A clinical photograph showing a skin lesion · referred with a clinical suspicion of melanoma — 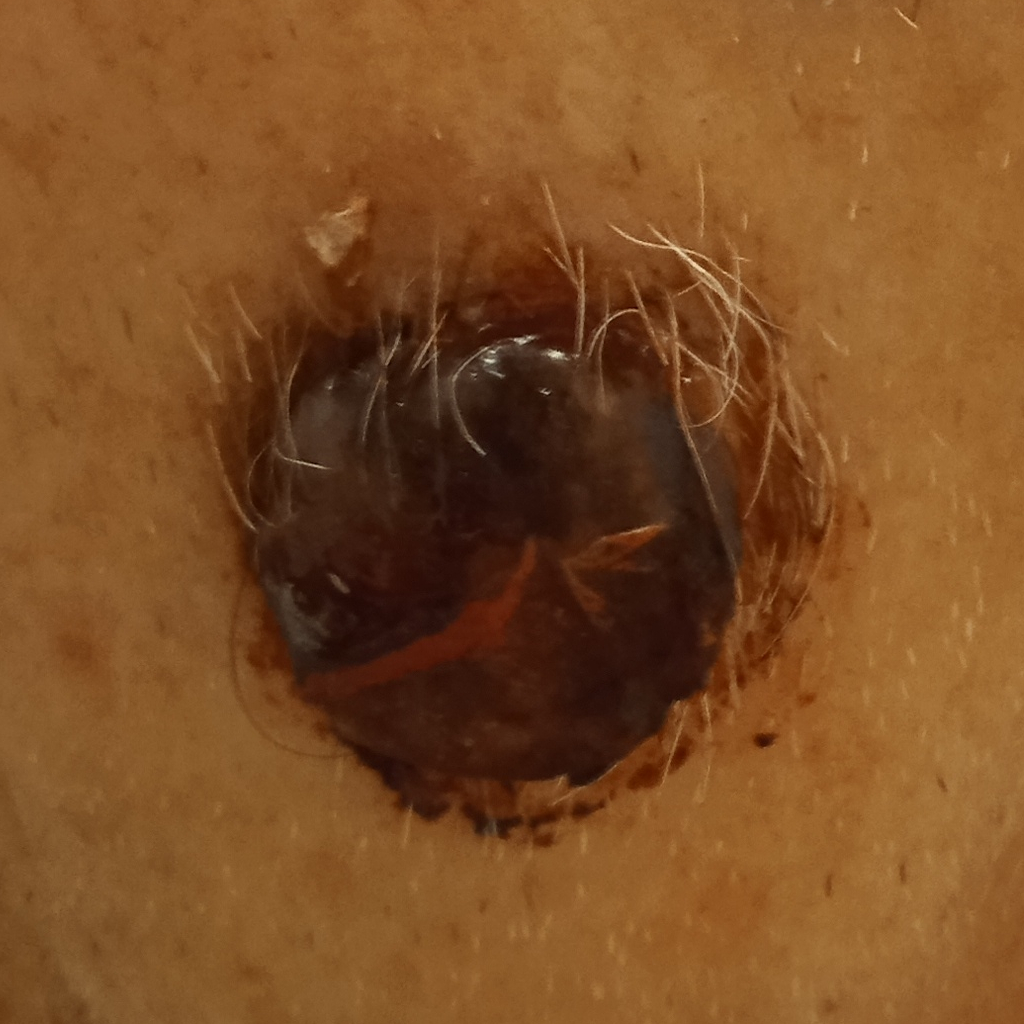| feature | finding |
|---|---|
| diameter | 19.9 mm |
| diagnosis | melanoma (biopsy-proven) |